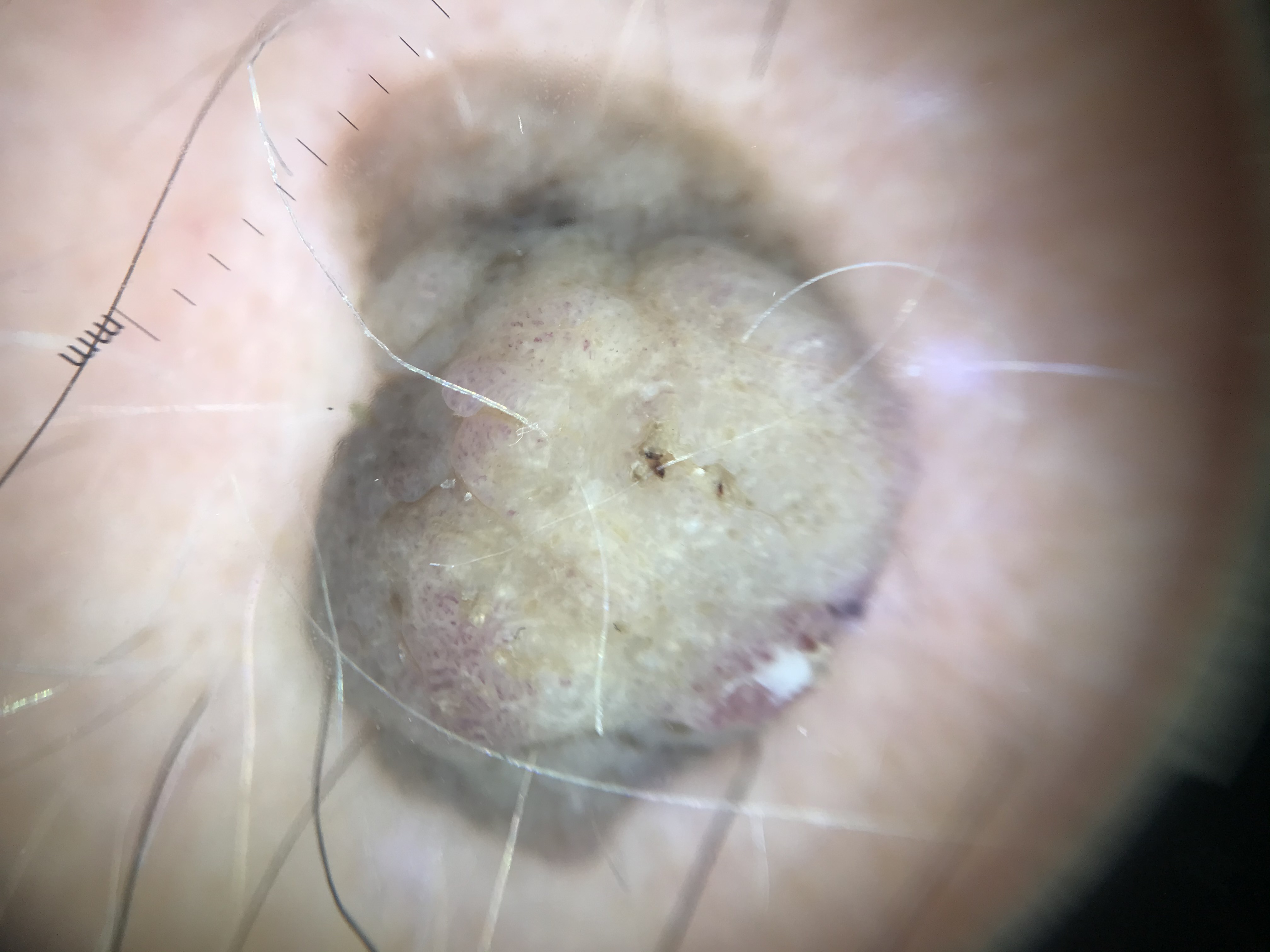classification = keratinocytic; diagnostic label = seborrheic keratosis (expert consensus).